Dermoscopy of a skin lesion.
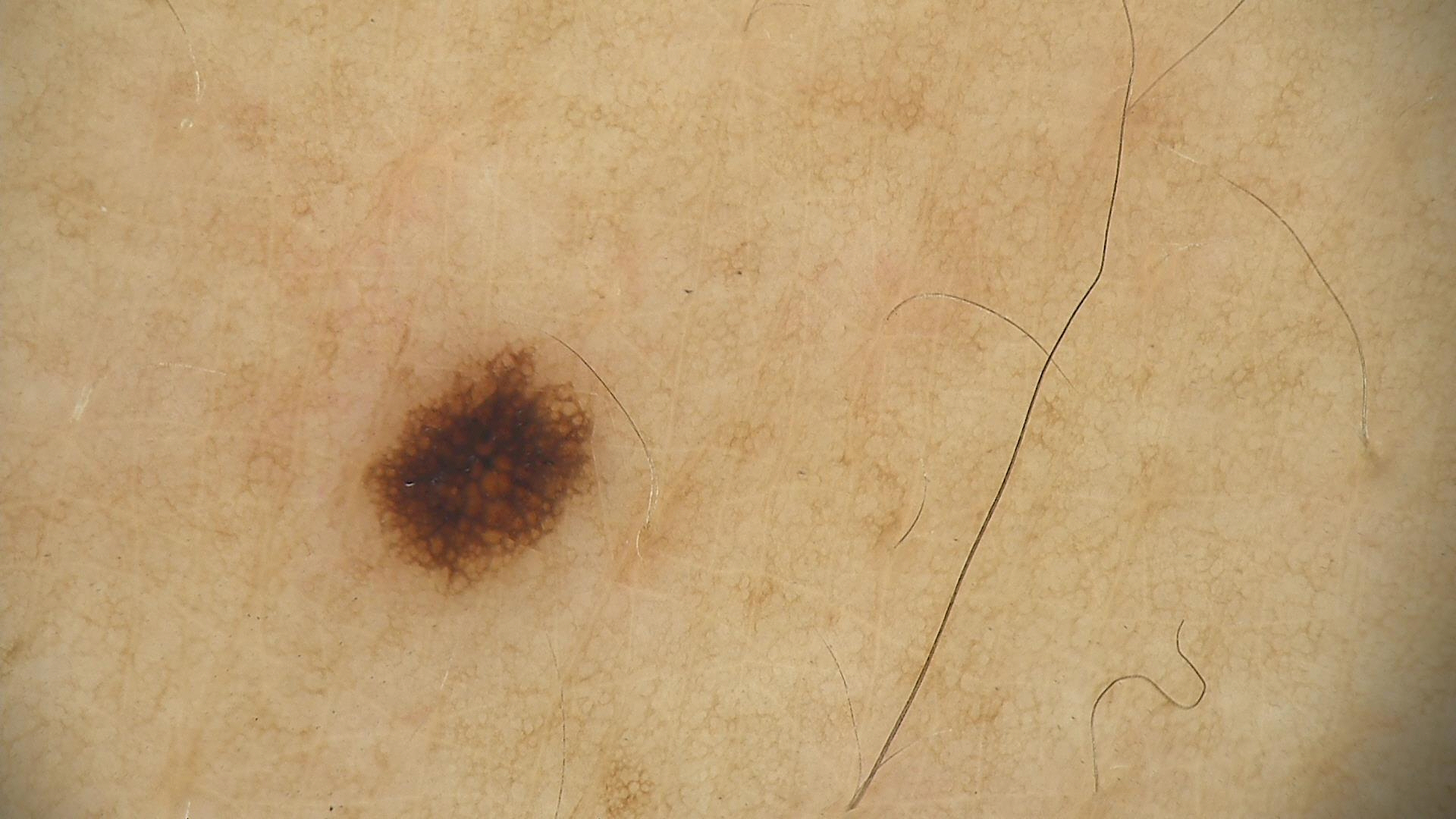Consistent with a dysplastic junctional nevus.